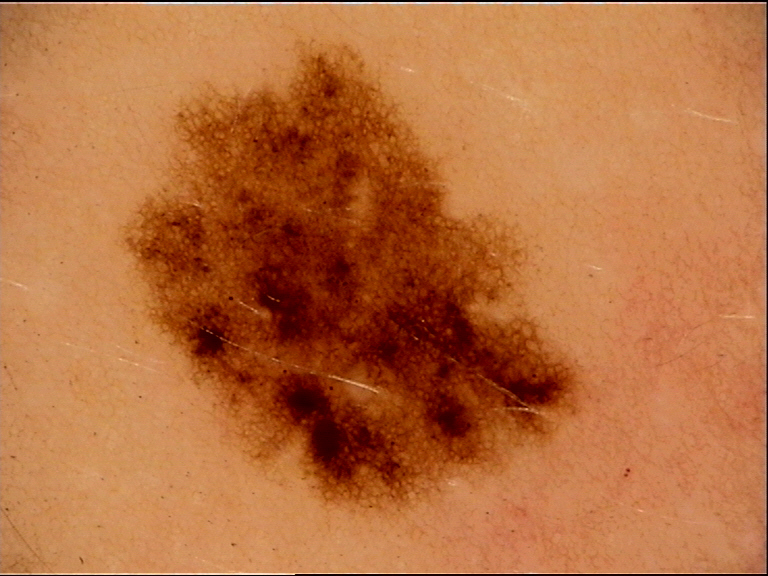Case:
Dermoscopy of a skin lesion.
Conclusion:
Classified as a benign lesion — a dysplastic junctional nevus.